The arm is involved, the photograph was taken at an angle, skin tone: Fitzpatrick skin type III, the contributor reports the lesion is flat and raised or bumpy, reported duration is one to four weeks, the lesion is associated with itching and burning: 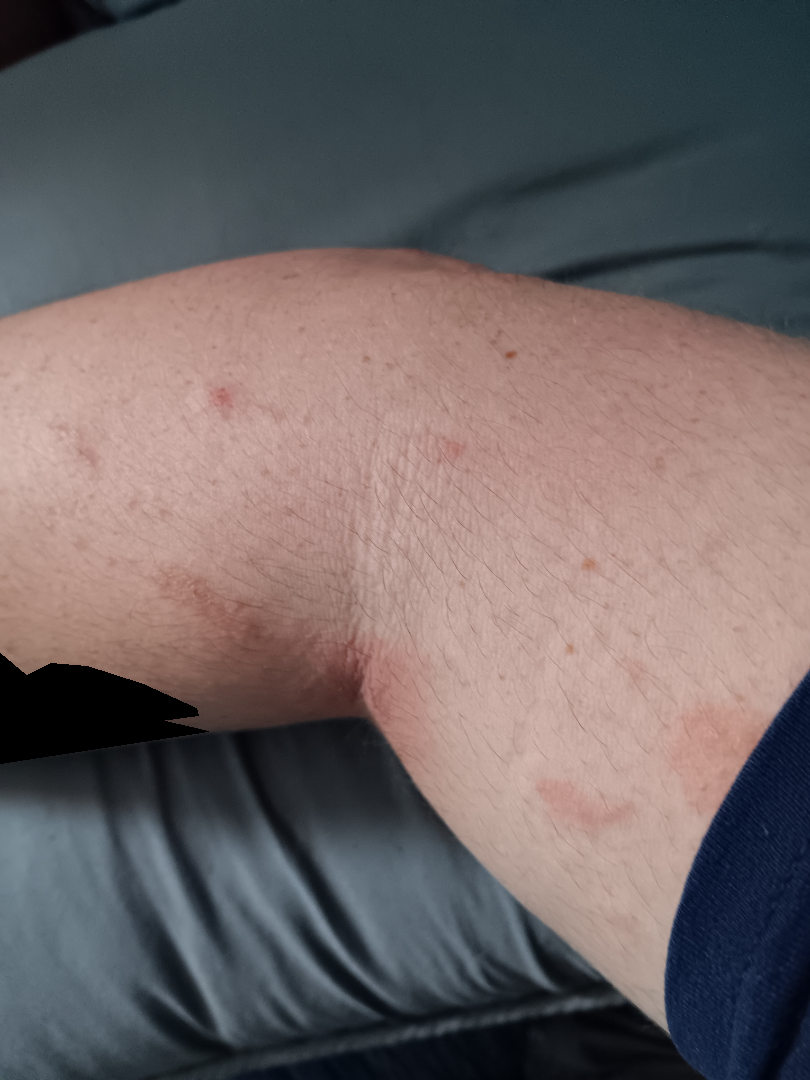Findings: On dermatologist assessment of the image: the leading impression is Eczema; also consider Tinea; also raised was Allergic Contact Dermatitis.